A close-up photograph:
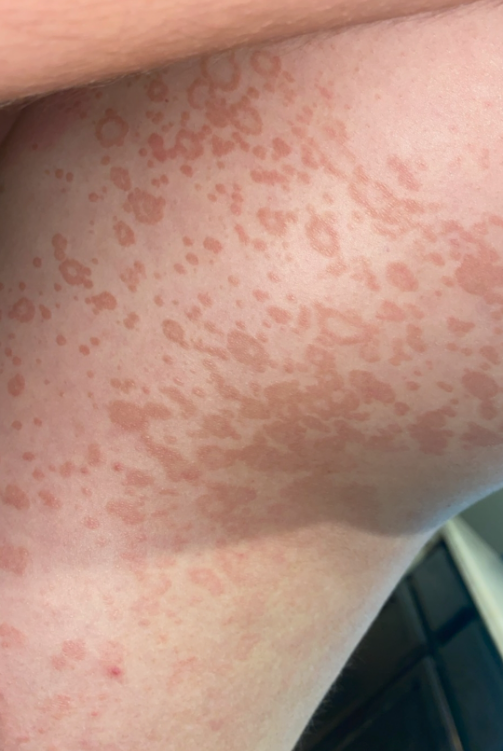Impression:
The image was not sufficient for the reviewer to characterize the skin condition.